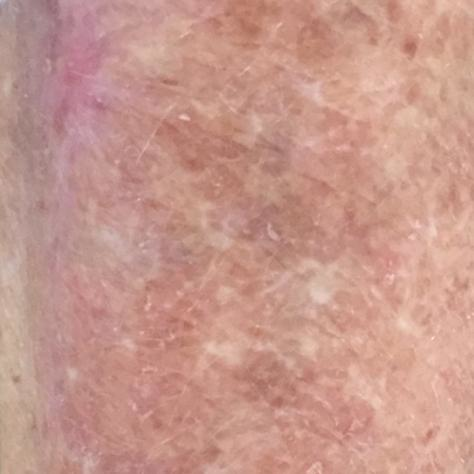A subject aged 66.
A clinical close-up photograph of a skin lesion.
The lesion involves an arm.
By the patient's account, the lesion itches and has grown.
The consensus clinical diagnosis was a lesion with uncertain malignant potential — an actinic keratosis.